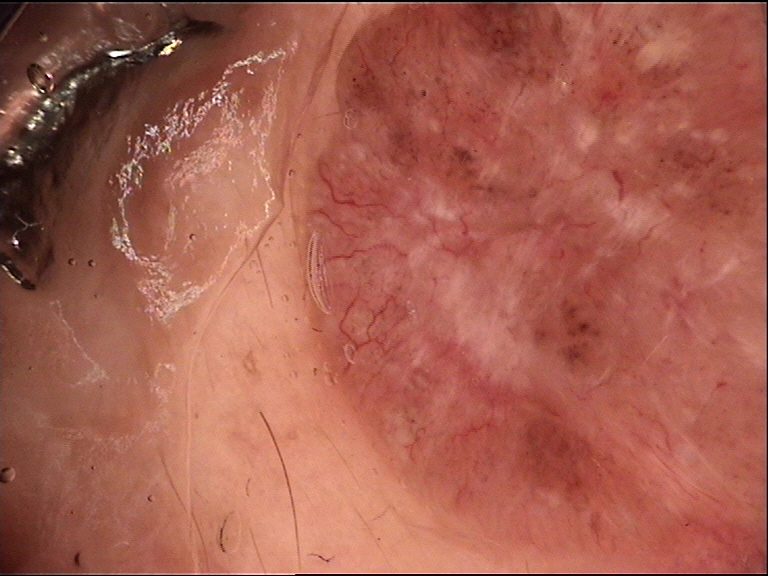diagnosis: basal cell carcinoma (biopsy-proven).